Close-up view — 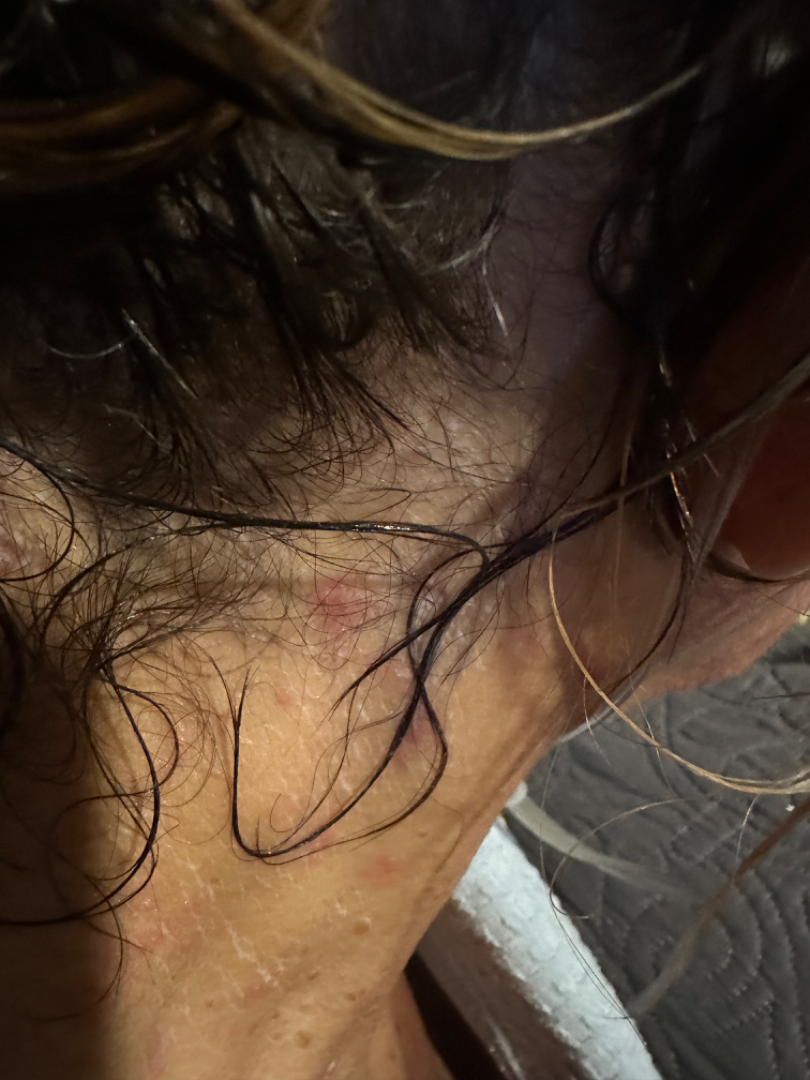Q: Could the case be diagnosed?
A: unable to determine